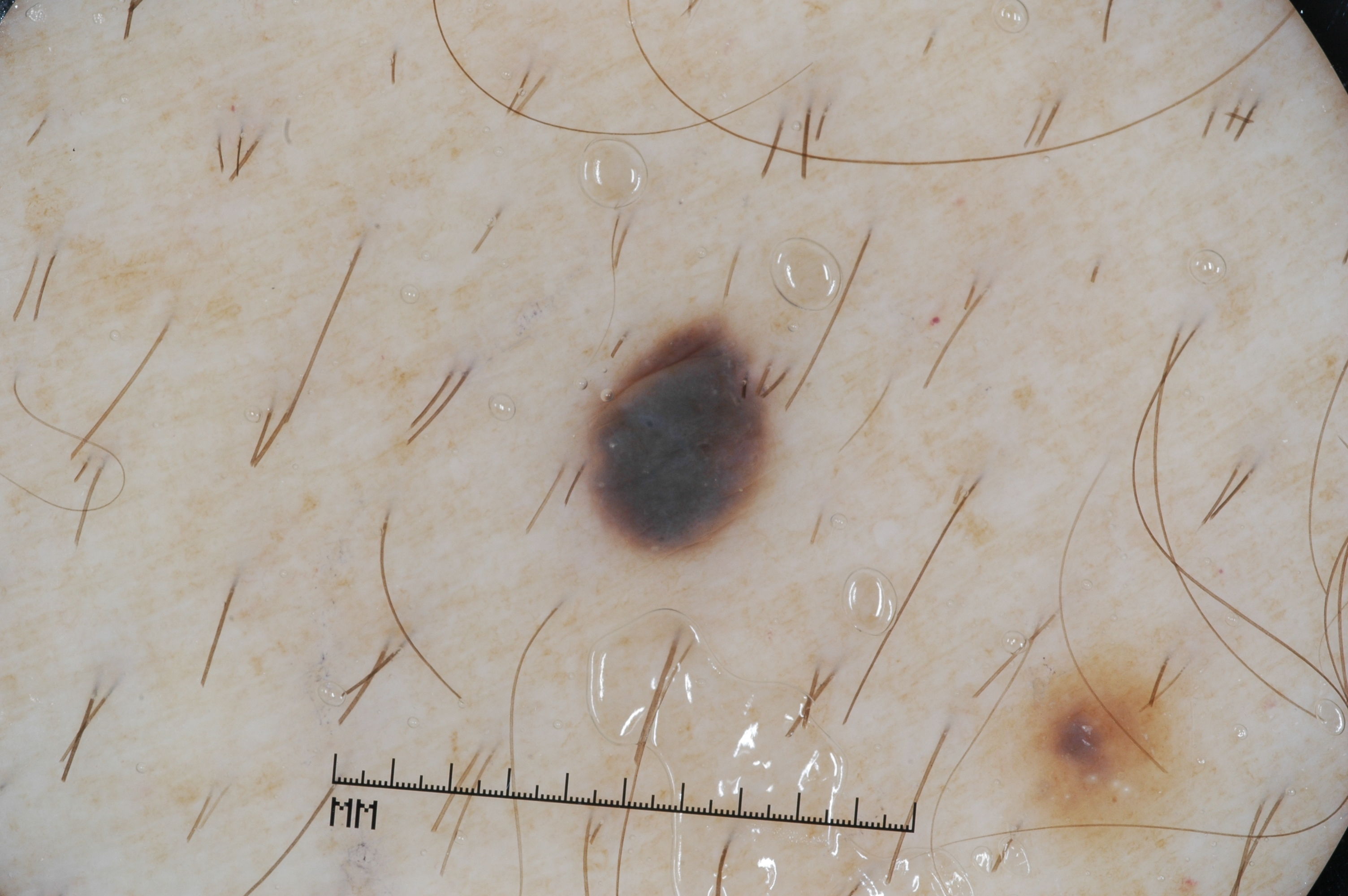  patient:
    sex: male
    age_approx: 55
  image:
    modality: dermoscopy
  dermoscopic_features:
    present:
      - milia-like cysts
    absent:
      - pigment network
      - negative network
      - streaks
  lesion_extent: small
  lesion_location:
    bbox_xyxy:
      - 579
      - 301
      - 776
      - 566
  diagnosis:
    name: melanocytic nevus
    malignancy: benign
    lineage: melanocytic
    provenance: clinical